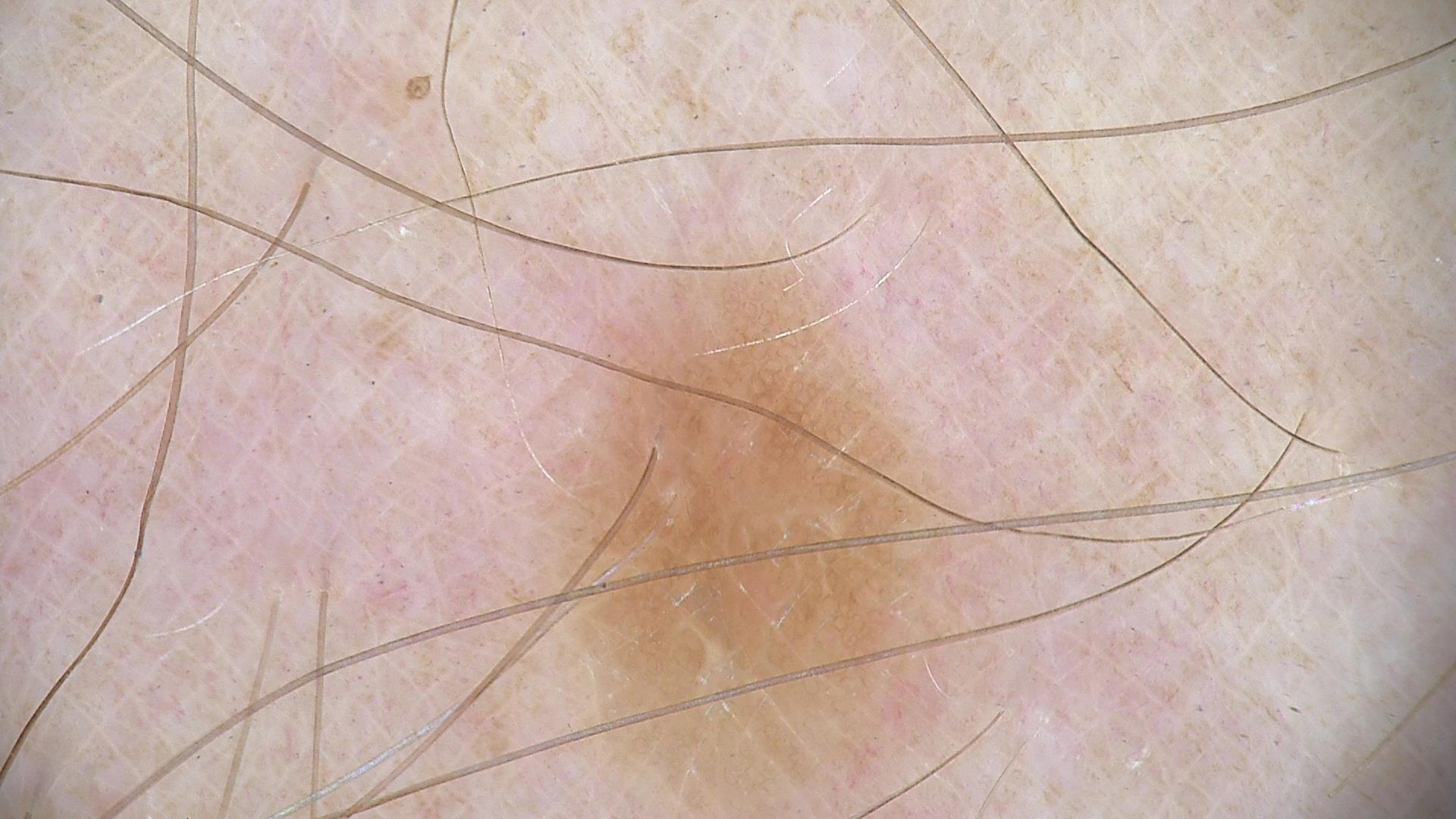The diagnostic label was a benign, fibro-histiocytic lesion — a dermatofibroma.